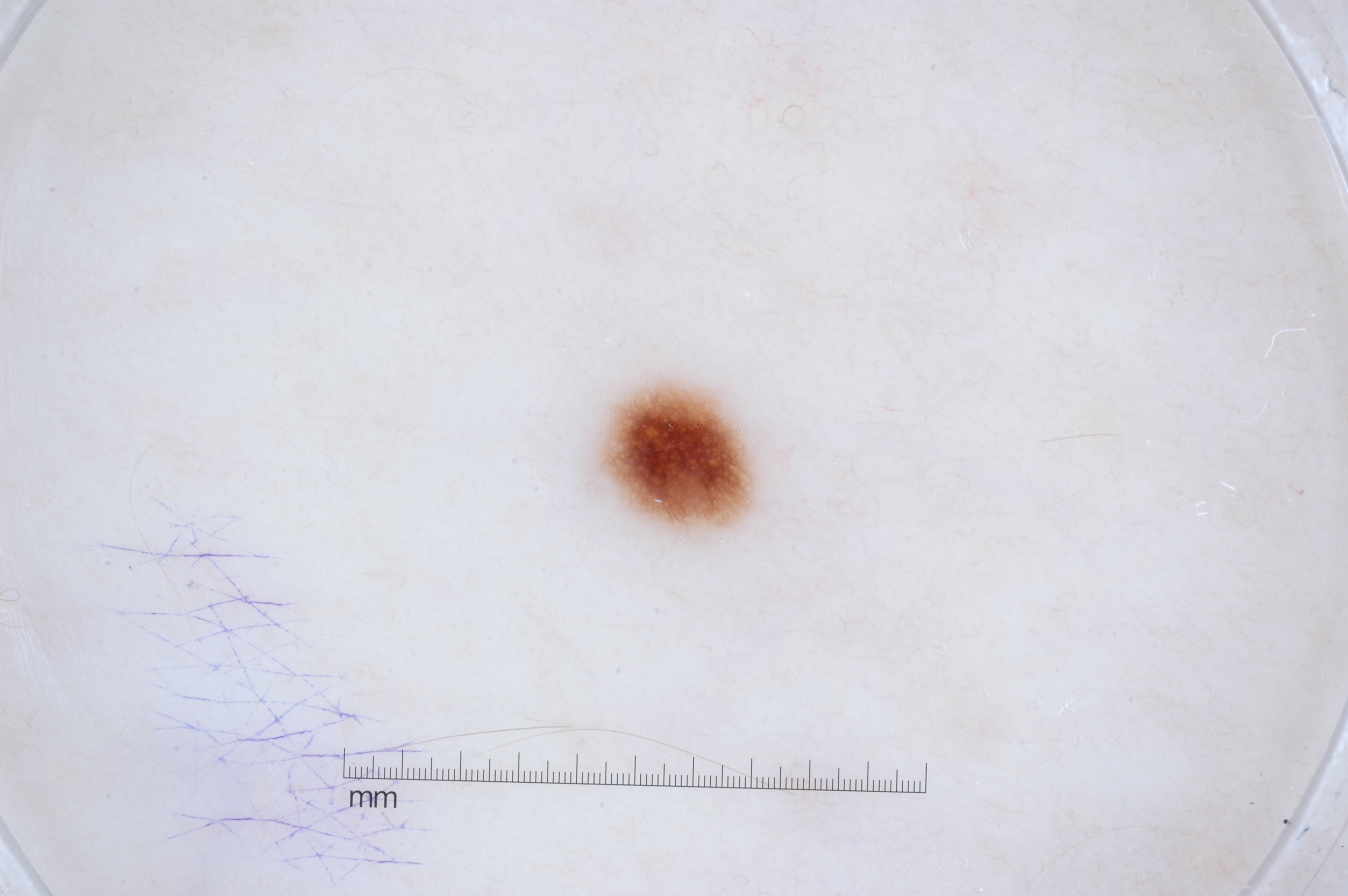<case>
  <patient>
    <sex>female</sex>
    <age_approx>45</age_approx>
  </patient>
  <image>
    <modality>dermoscopy</modality>
  </image>
  <dermoscopic_features>
    <present>pigment network</present>
    <absent>milia-like cysts, streaks, negative network</absent>
  </dermoscopic_features>
  <lesion_location>
    <bbox_xyxy>601, 385, 758, 532</bbox_xyxy>
  </lesion_location>
  <diagnosis>
    <name>melanocytic nevus</name>
    <malignancy>benign</malignancy>
    <lineage>melanocytic</lineage>
    <provenance>clinical</provenance>
  </diagnosis>
</case>